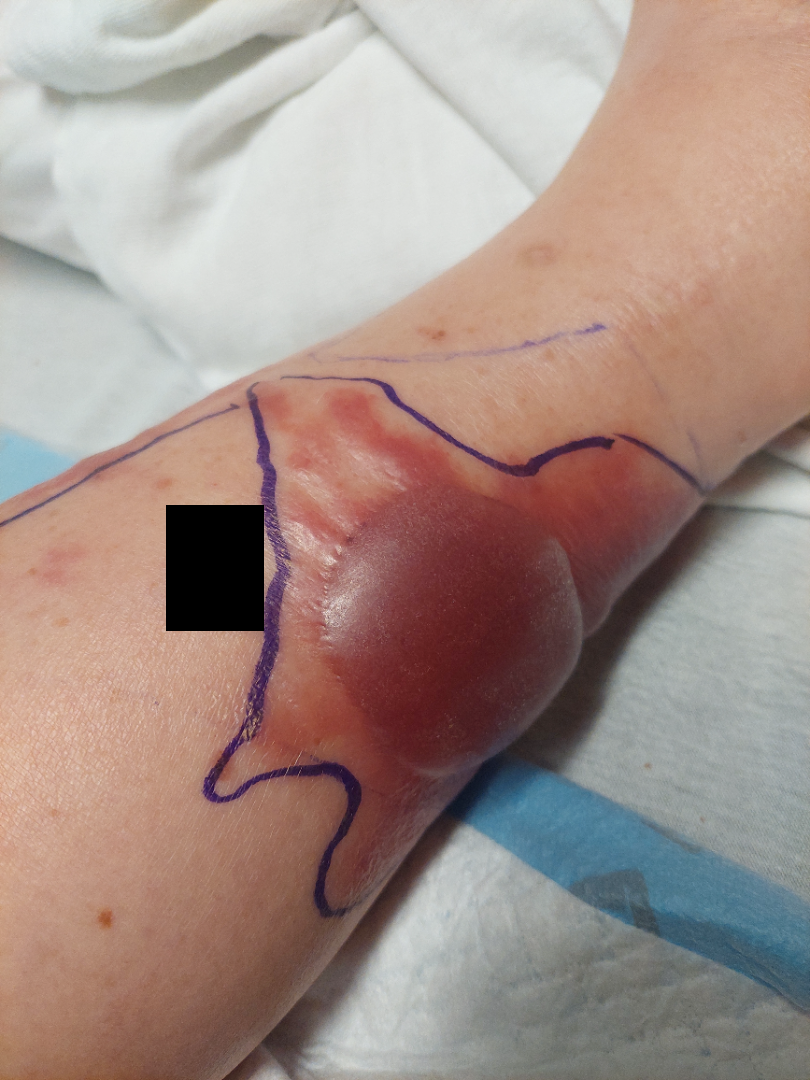| field | value |
|---|---|
| site | leg and top or side of the foot |
| skin tone | Fitzpatrick skin type II |
| reported symptoms | burning and bothersome appearance |
| duration | one to four weeks |
| subject | female, age 50–59 |
| other reported symptoms | shortness of breath, fatigue and fever |
| patient describes the issue as | a rash |
| view | close-up |
| diagnostic considerations | the differential is split between Skin and soft tissue atypical mycobacterial infection and hemorrhagic bullae; less likely is Bullous dermatitis, NOS |